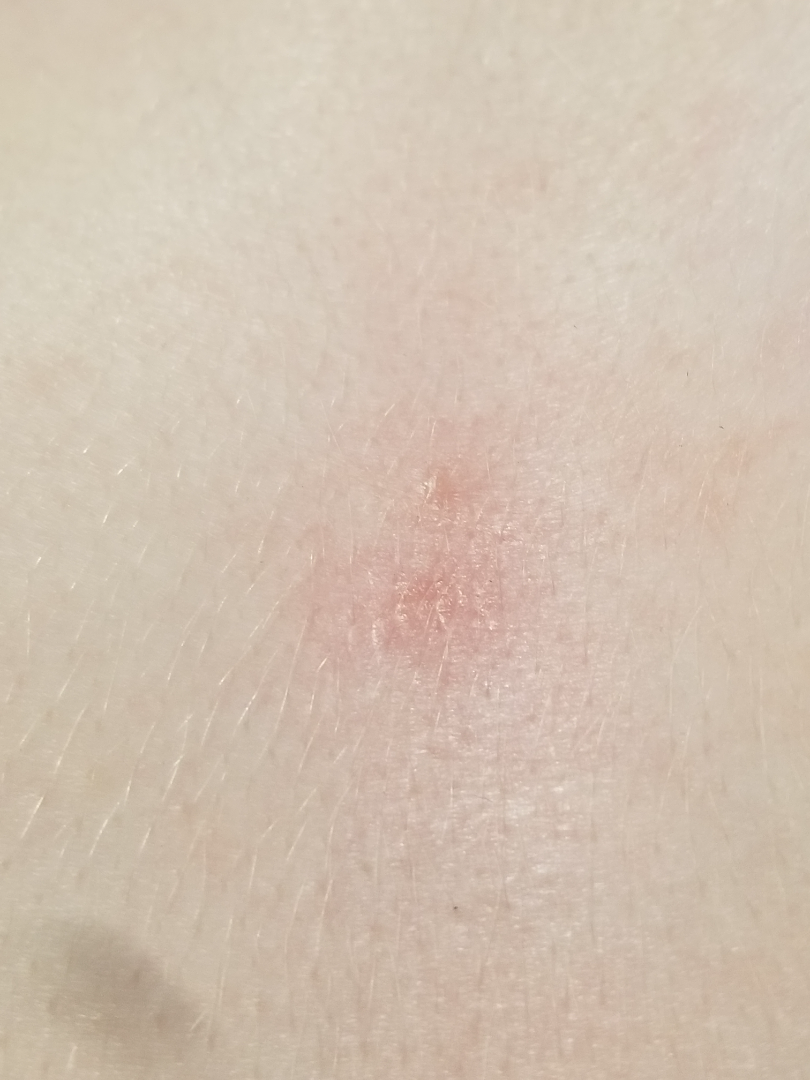No differential diagnosis could be assigned on photographic review.